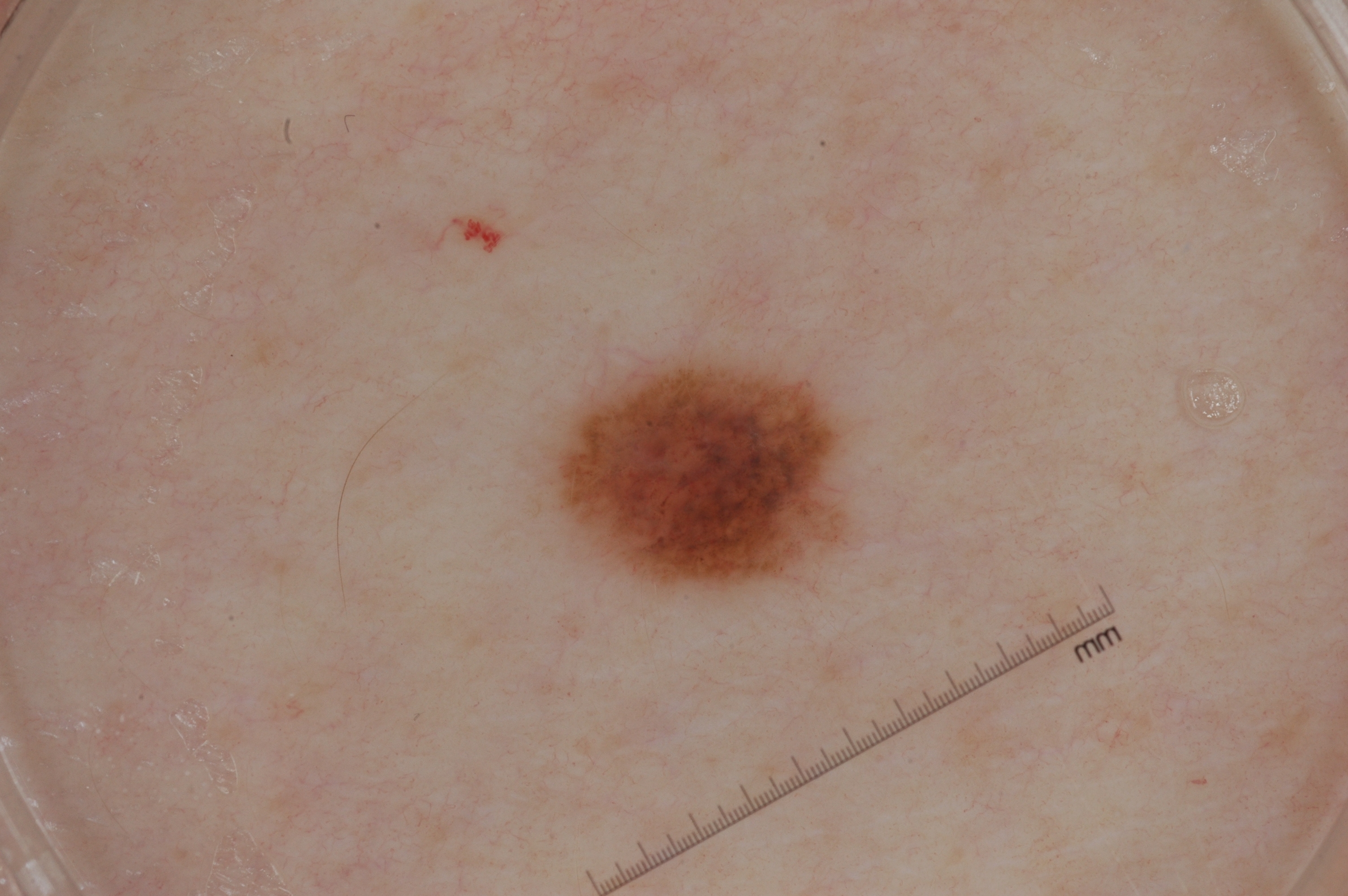A male subject, about 30 years old.
A dermoscopic close-up of a skin lesion.
The lesion takes up about 5% of the image.
As (left, top, right, bottom), the lesion's extent is <box>548, 357, 842, 588</box>.
Dermoscopy demonstrates no negative network, milia-like cysts, streaks, or pigment network.
Histopathologically confirmed as a melanoma.